Skin tone: non-clinician graders estimated a Monk skin tone scale of 2. Close-up view:
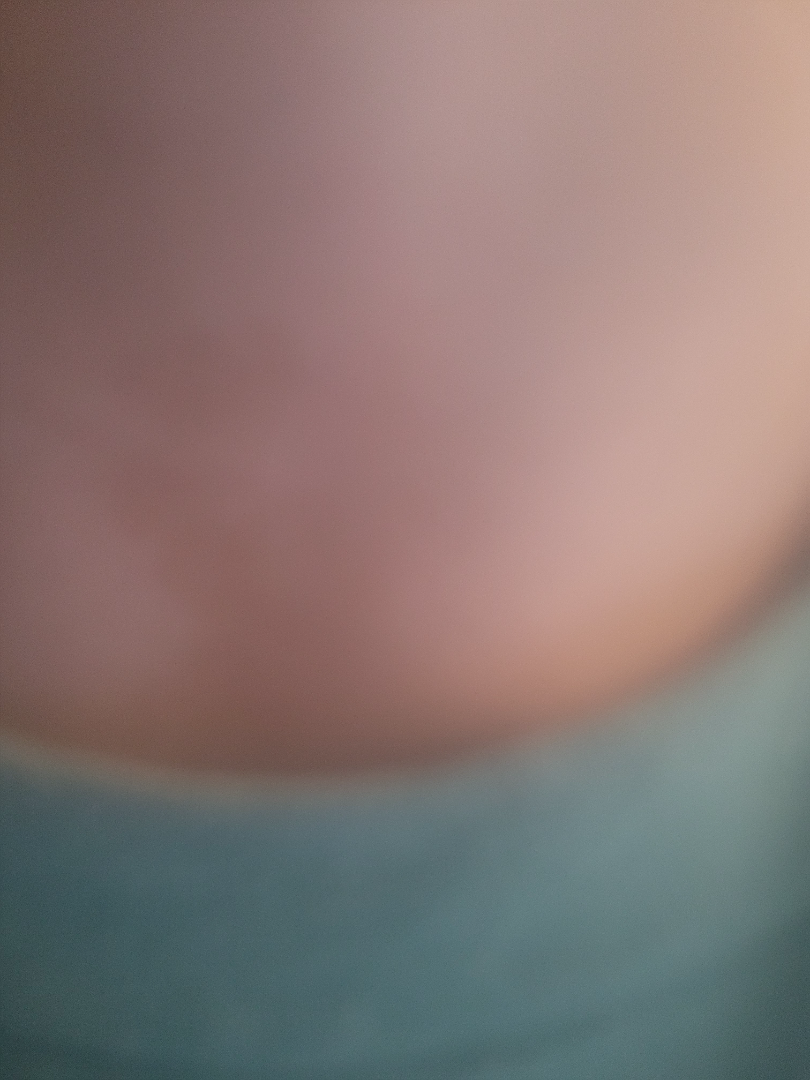<case>
  <assessment>could not be assessed</assessment>
</case>